Dermoscopy of a skin lesion.
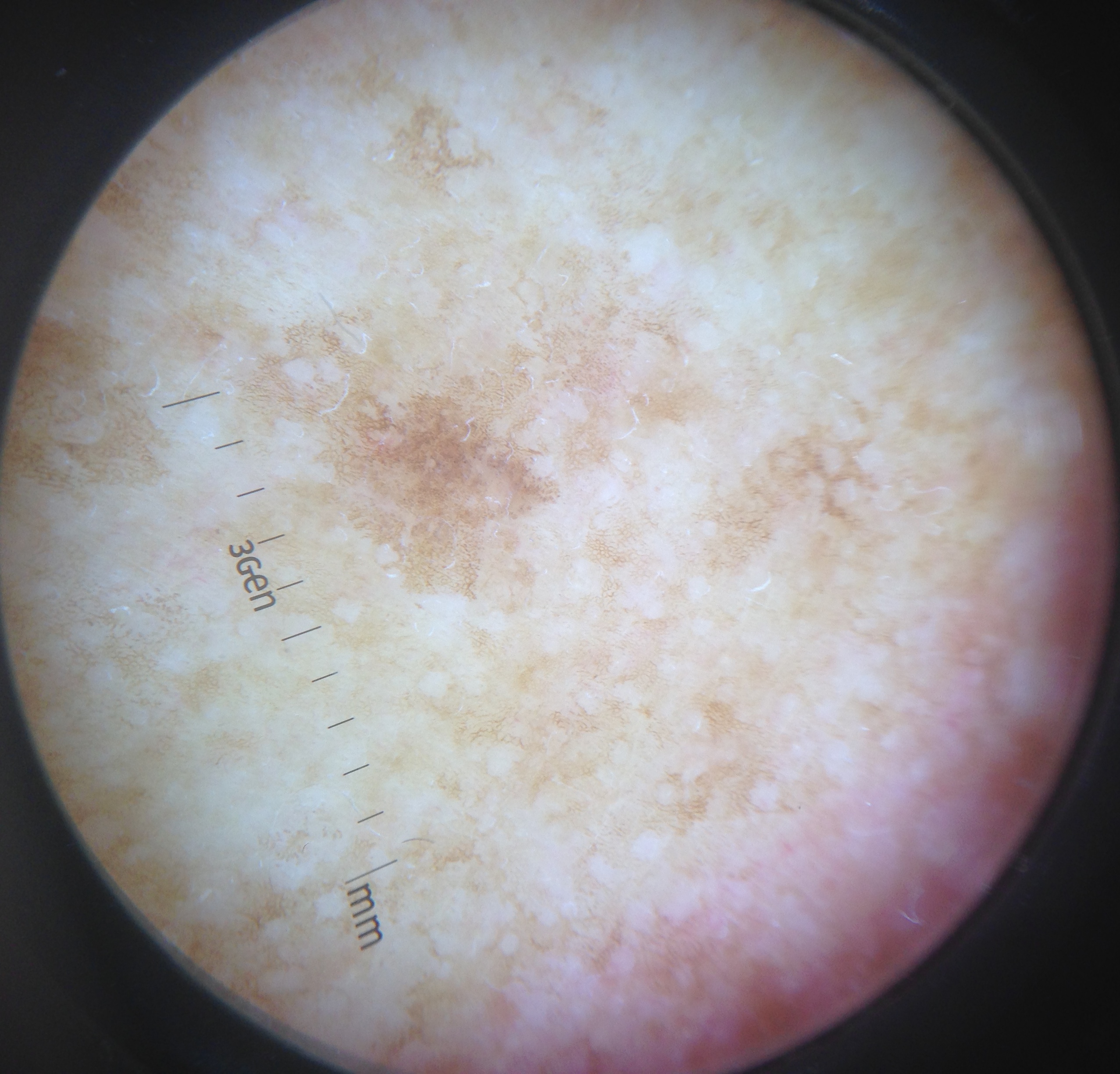Findings:
- assessment · solar lentigo (expert consensus)